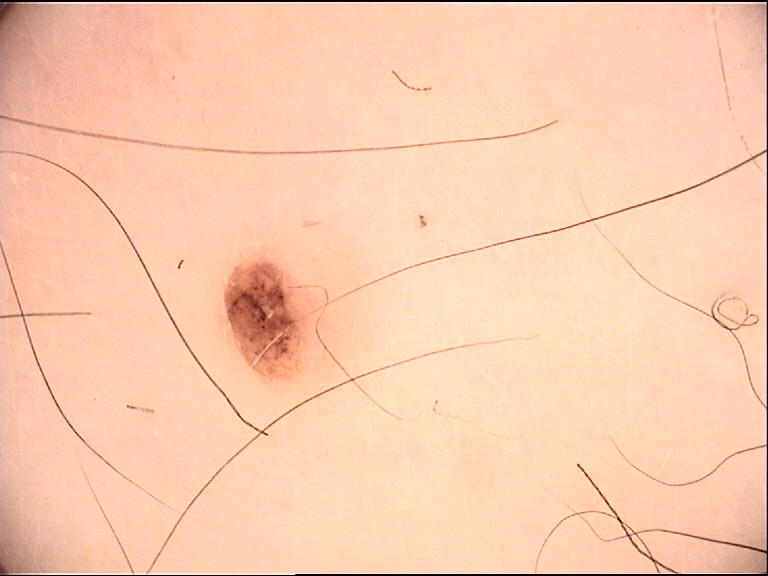{"image": "dermoscopy", "lesion_type": {"main_class": "banal", "pattern": "dermal"}, "diagnosis": {"name": "dermal nevus", "code": "db", "malignancy": "benign", "super_class": "melanocytic", "confirmation": "expert consensus"}}